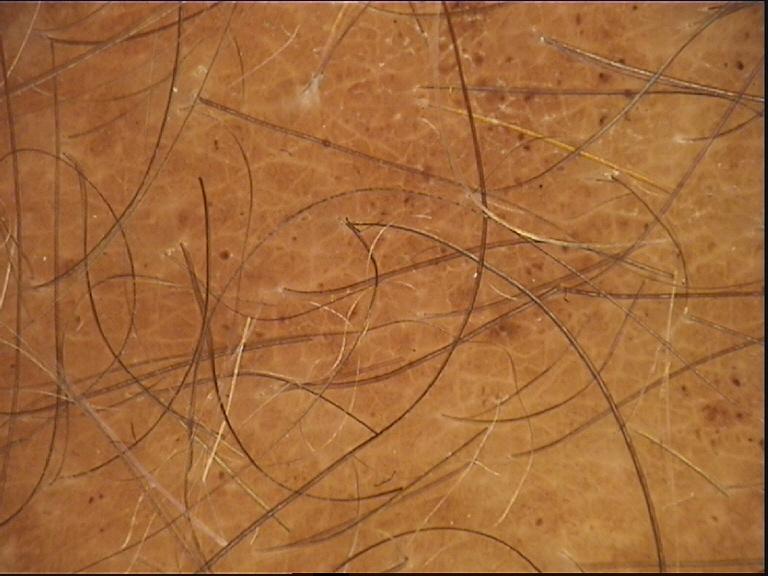Conclusion:
Consistent with a congenital compound nevus.